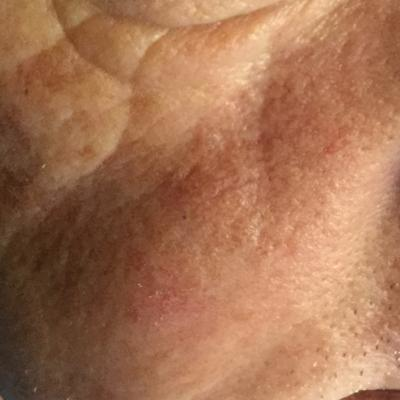Q: Tell me about the patient.
A: age 54
Q: How was this image acquired?
A: clinical photo
Q: What symptoms does the patient report?
A: bleeding, itching
Q: What is the diagnosis?
A: actinic keratosis (clinical consensus)